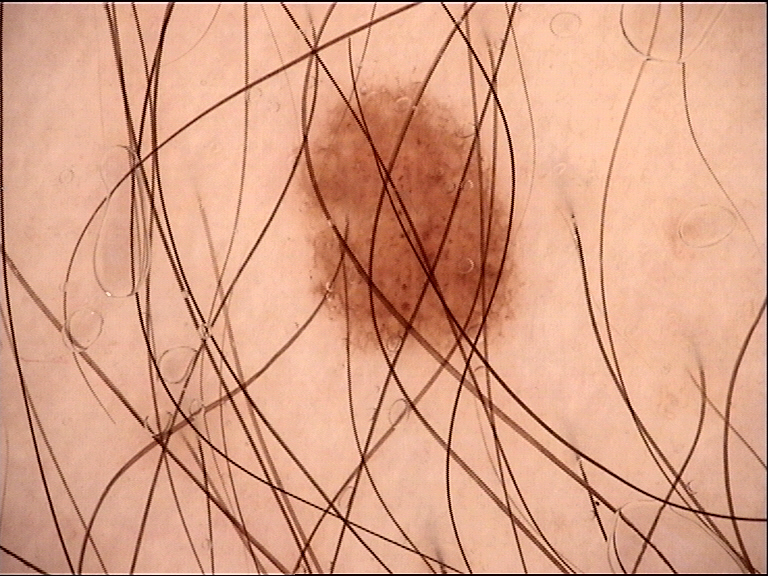image: dermatoscopy
assessment: dysplastic junctional nevus (expert consensus)